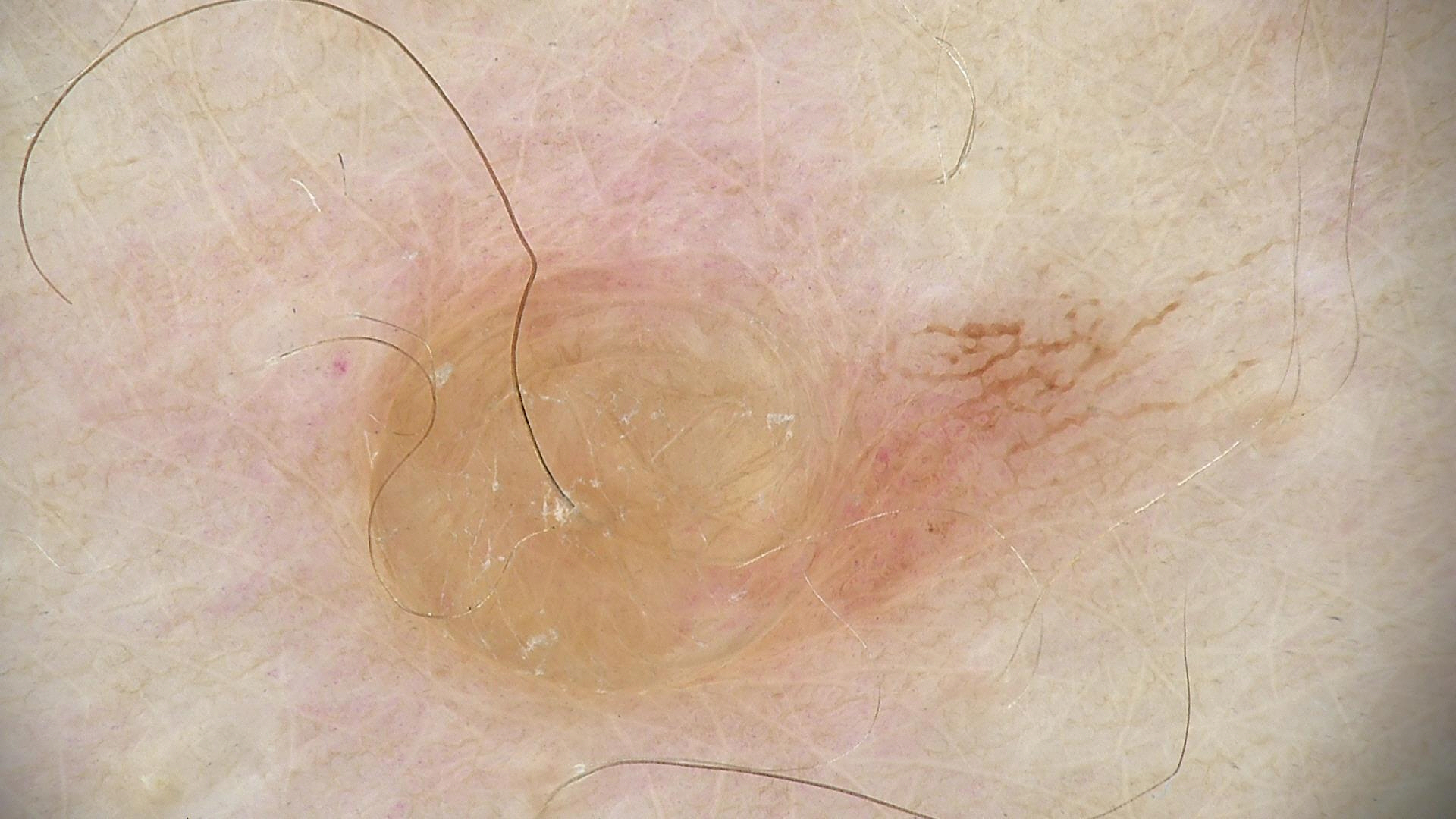A dermoscopic image of a skin lesion.
The morphology is that of a banal lesion.
Classified as a dermal nevus.